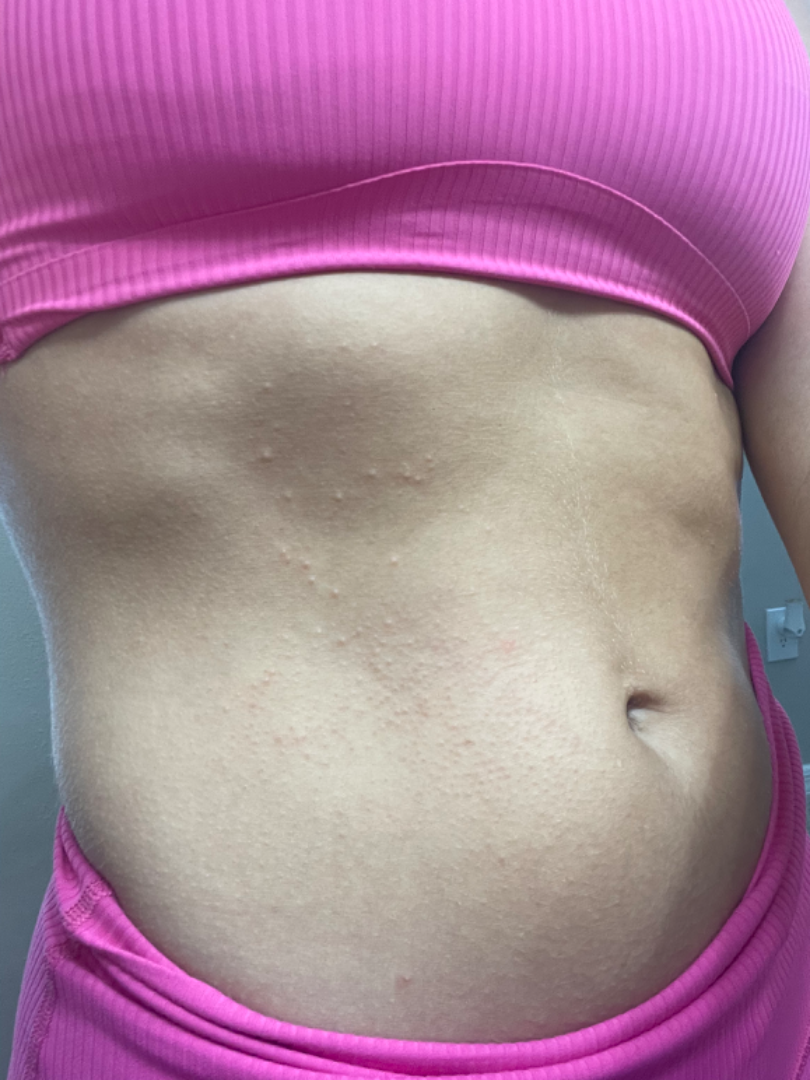assessment — ungradable on photographic review
described texture — raised or bumpy
duration — one to four weeks
framing — close-up
patient — female
affected area — front of the torso
patient describes the issue as — a rash